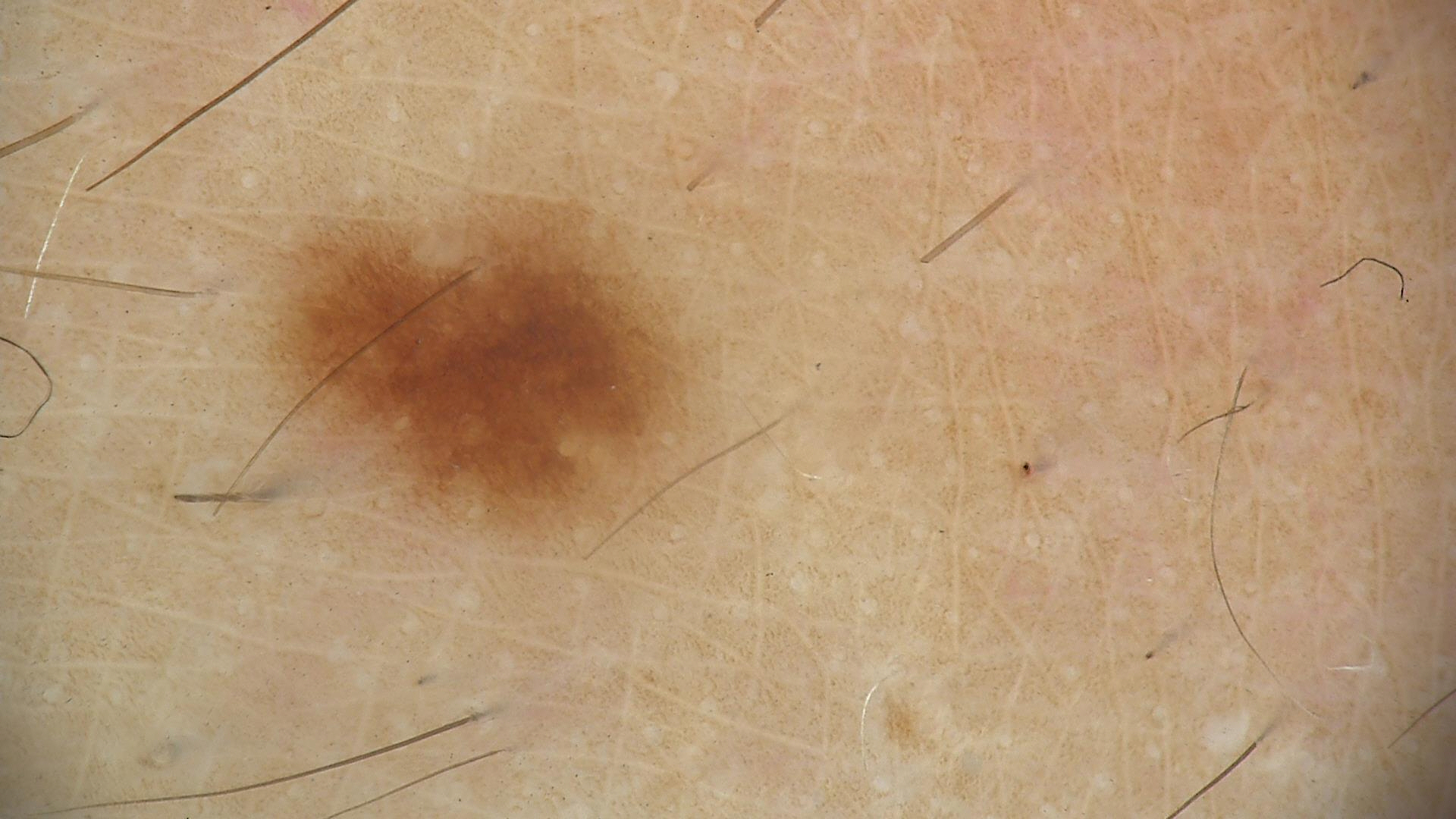image = dermoscopy
diagnostic label = dysplastic junctional nevus (expert consensus)